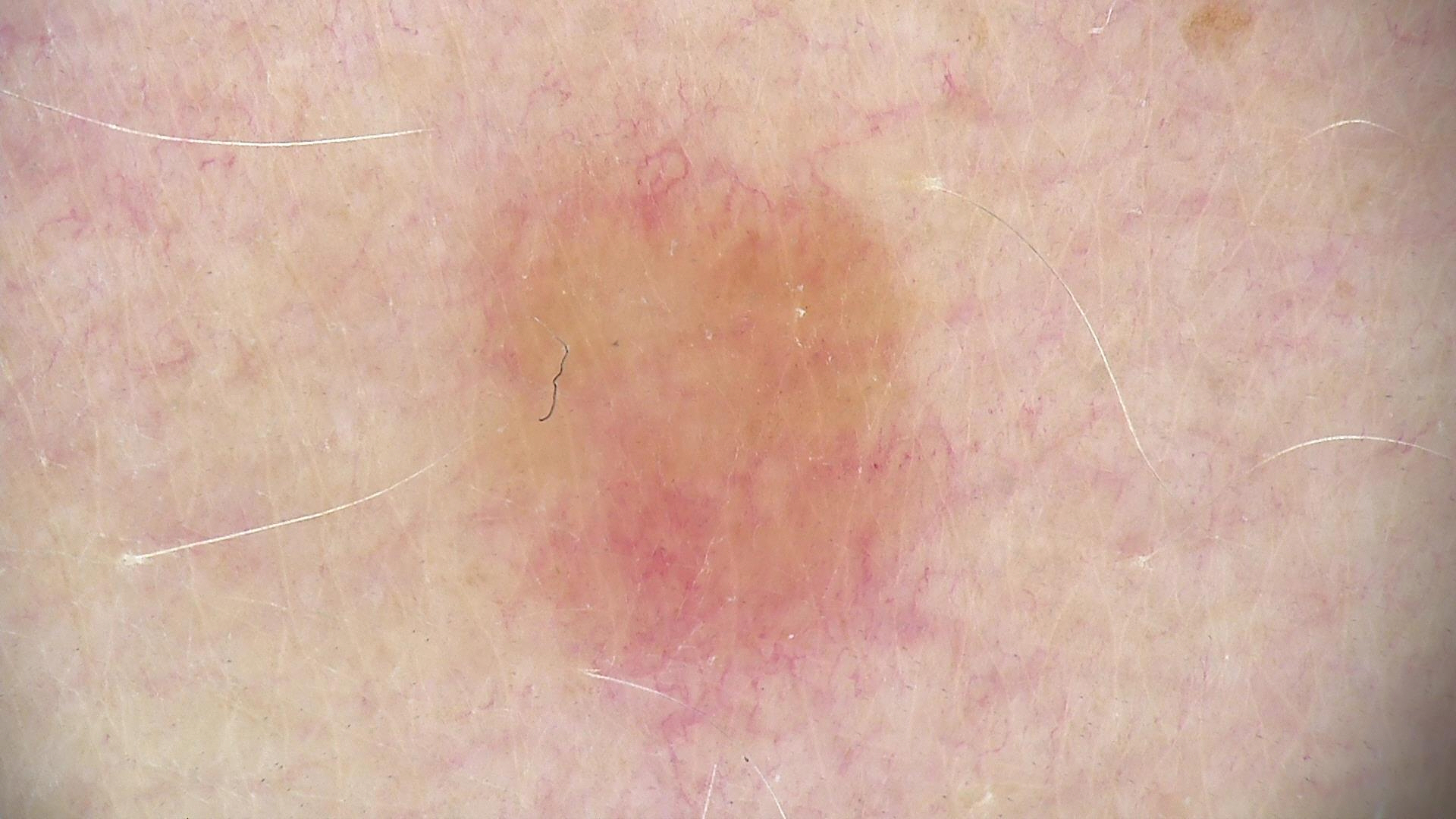<dermoscopy>
<diagnosis>
<name>junctional nevus</name>
<code>jb</code>
<malignancy>benign</malignancy>
<super_class>melanocytic</super_class>
<confirmation>expert consensus</confirmation>
</diagnosis>
</dermoscopy>